A skin lesion imaged with a dermatoscope: 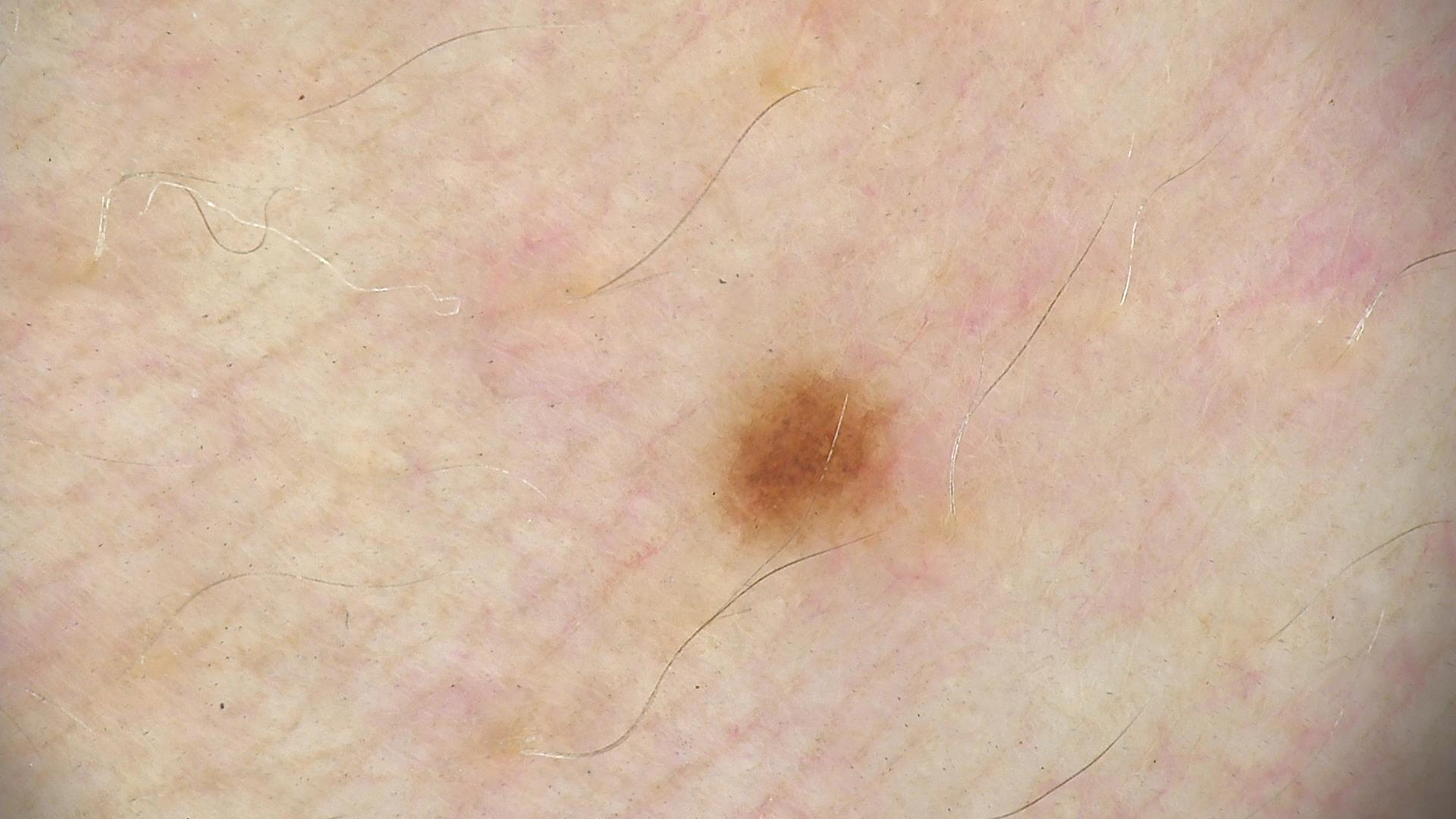Classified as a dysplastic junctional nevus.